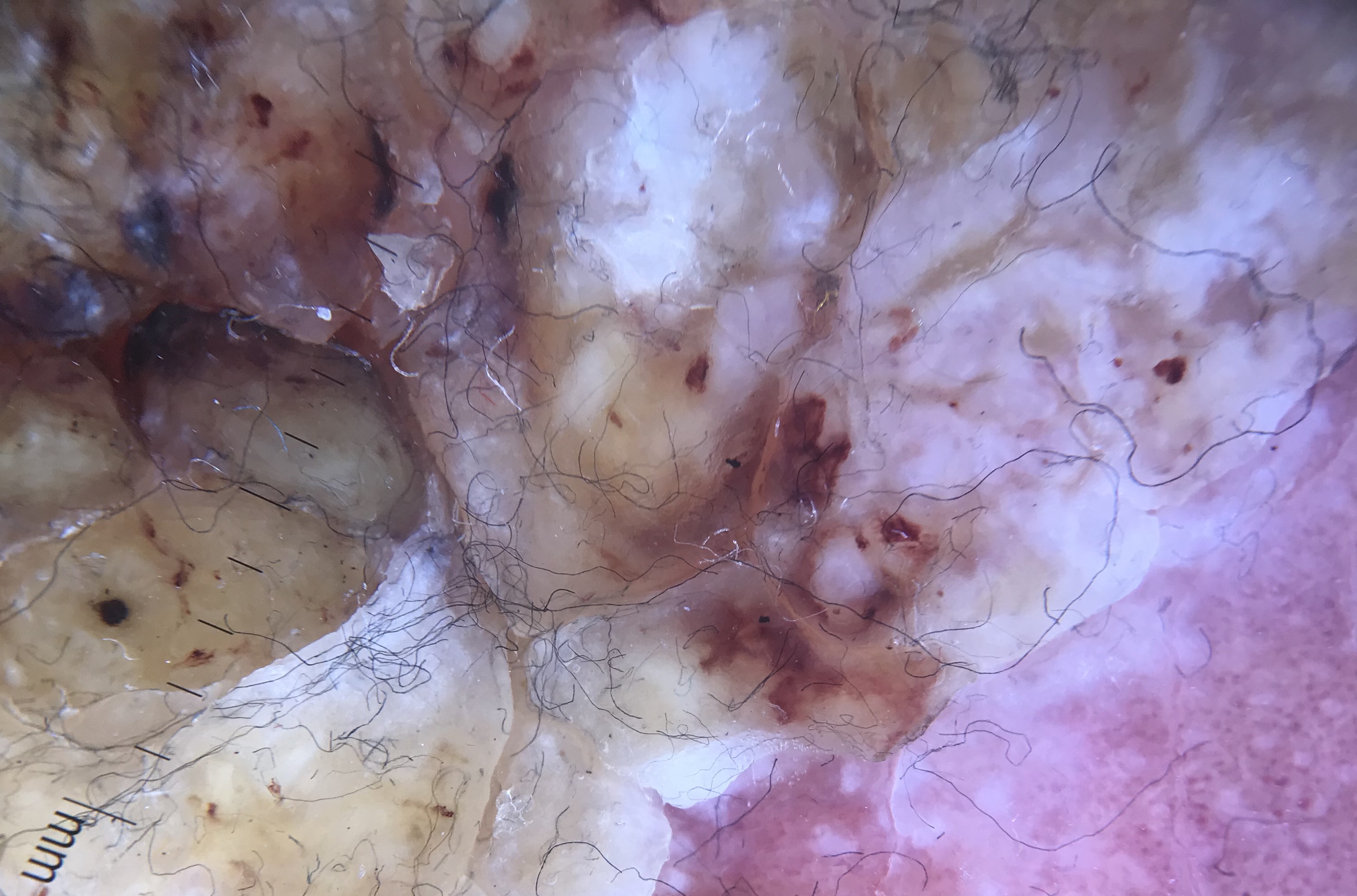A dermoscopy image of a single skin lesion.
The morphology is that of a keratinocytic lesion.
The biopsy diagnosis was a malignancy — a squamous cell carcinoma.